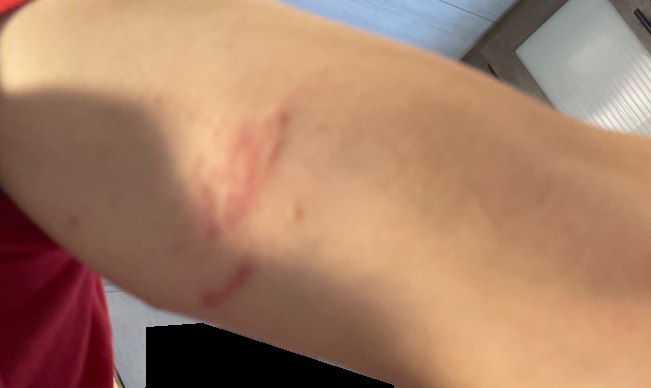Clinical context:
Close-up view. Skin tone: Fitzpatrick skin type III; lay reviewers estimated a Monk skin tone scale of 3.
Assessment:
Consistent with Scar Condition.